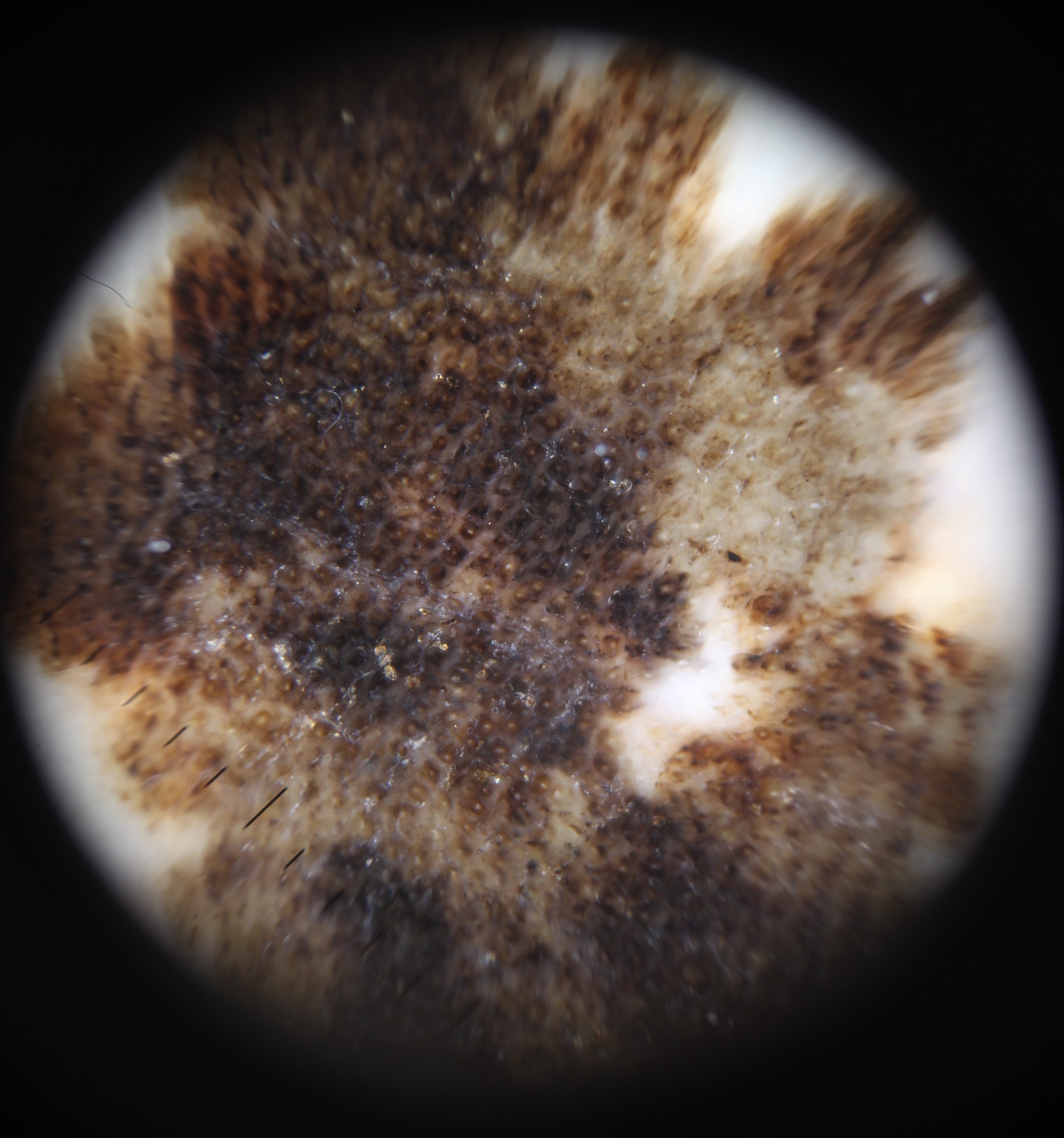Histopathology confirmed an acral lentiginous melanoma.